The subject is a male aged 60–69 · an image taken at an angle.
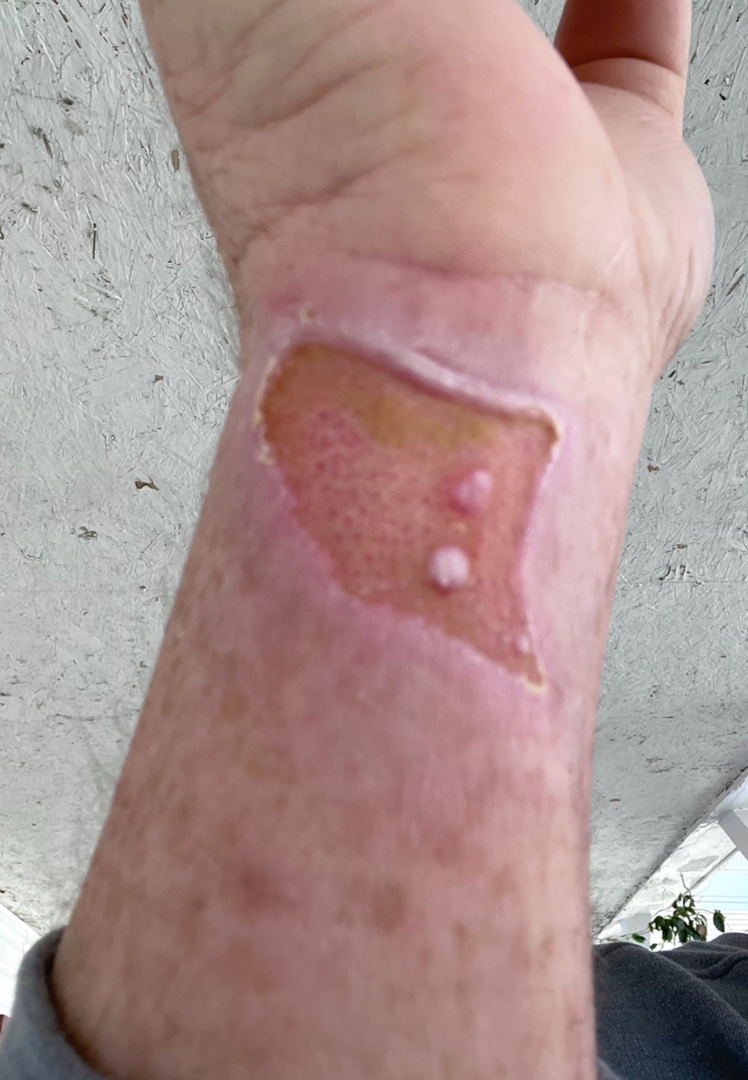assessment: not assessable.